A dermoscopic image of a skin lesion: 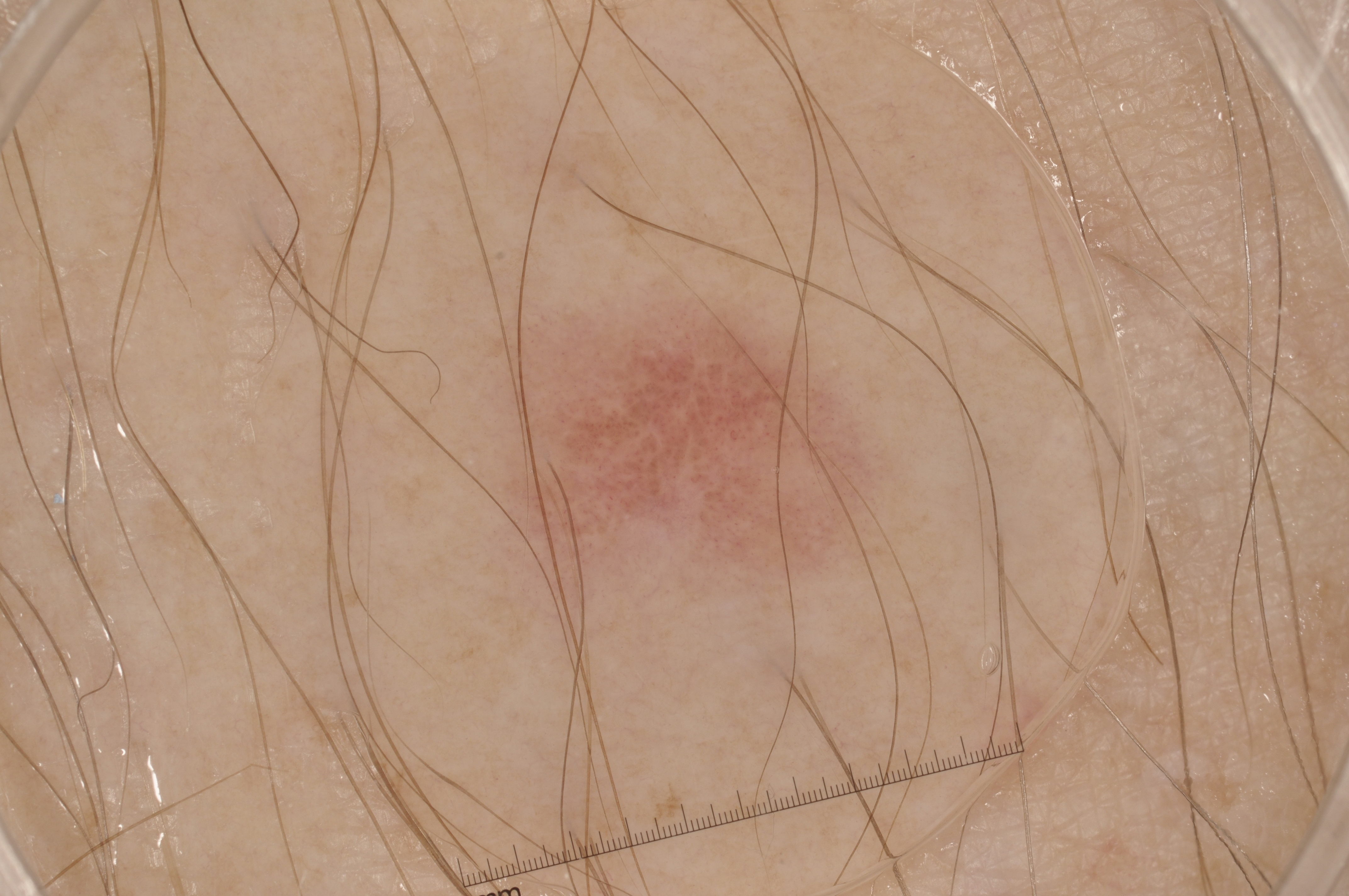location = left=506, top=309, right=875, bottom=574 | features = negative network; absent: pigment network, milia-like cysts, and streaks | impression = a melanoma.